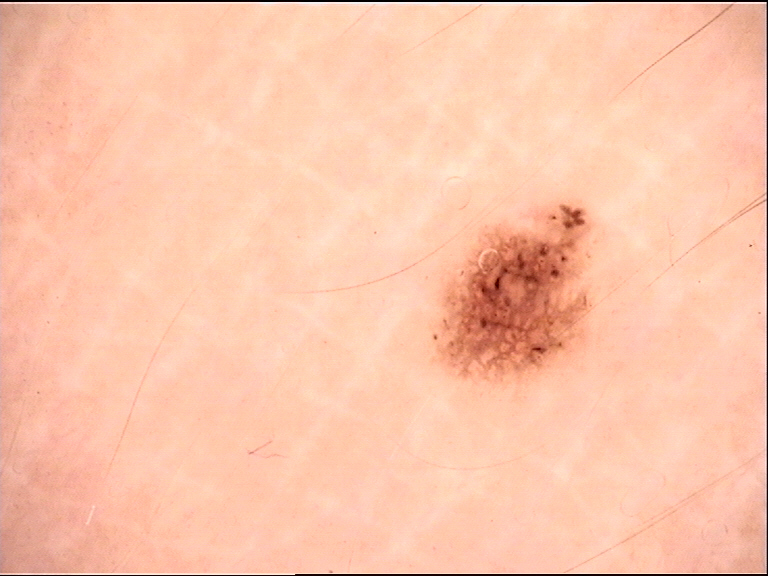Findings:
- diagnosis — dysplastic junctional nevus (expert consensus)